The condition has been present for one to four weeks · skin tone: self-reported FST II · the lesion is described as raised or bumpy · the patient is 18–29, female · the photo was captured at an angle · the arm and back of the hand are involved:
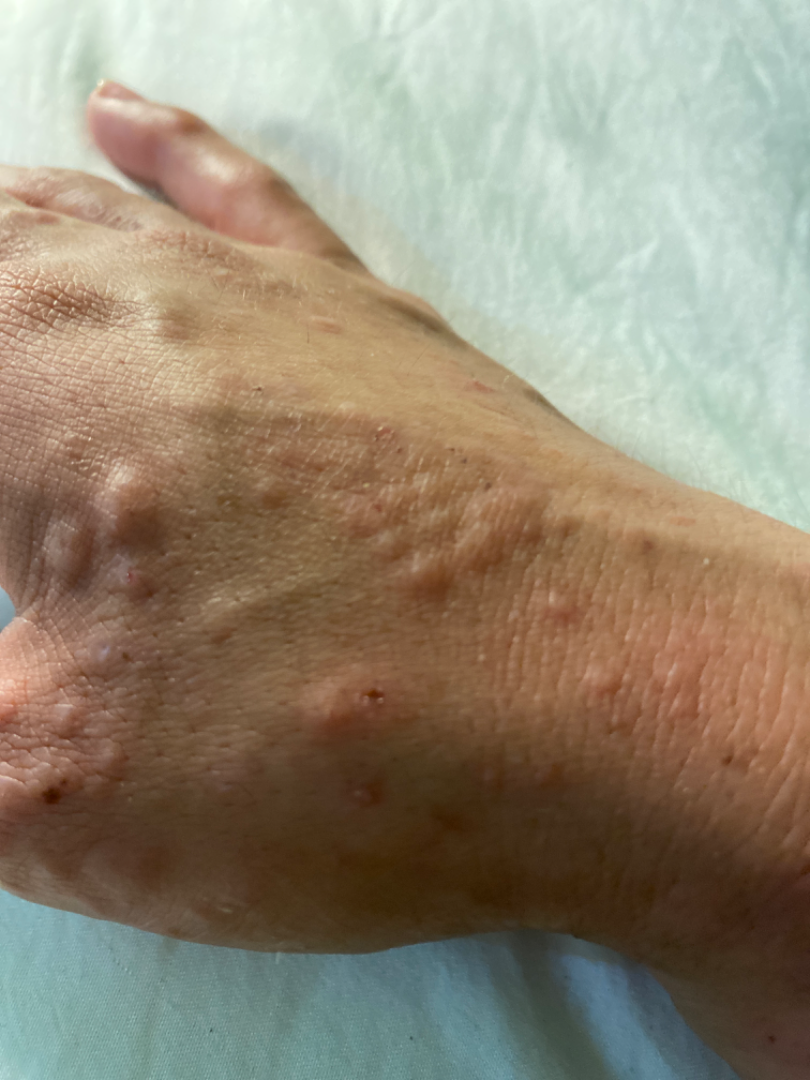Findings: Diagnostic features were not clearly distinguishable in this photograph.